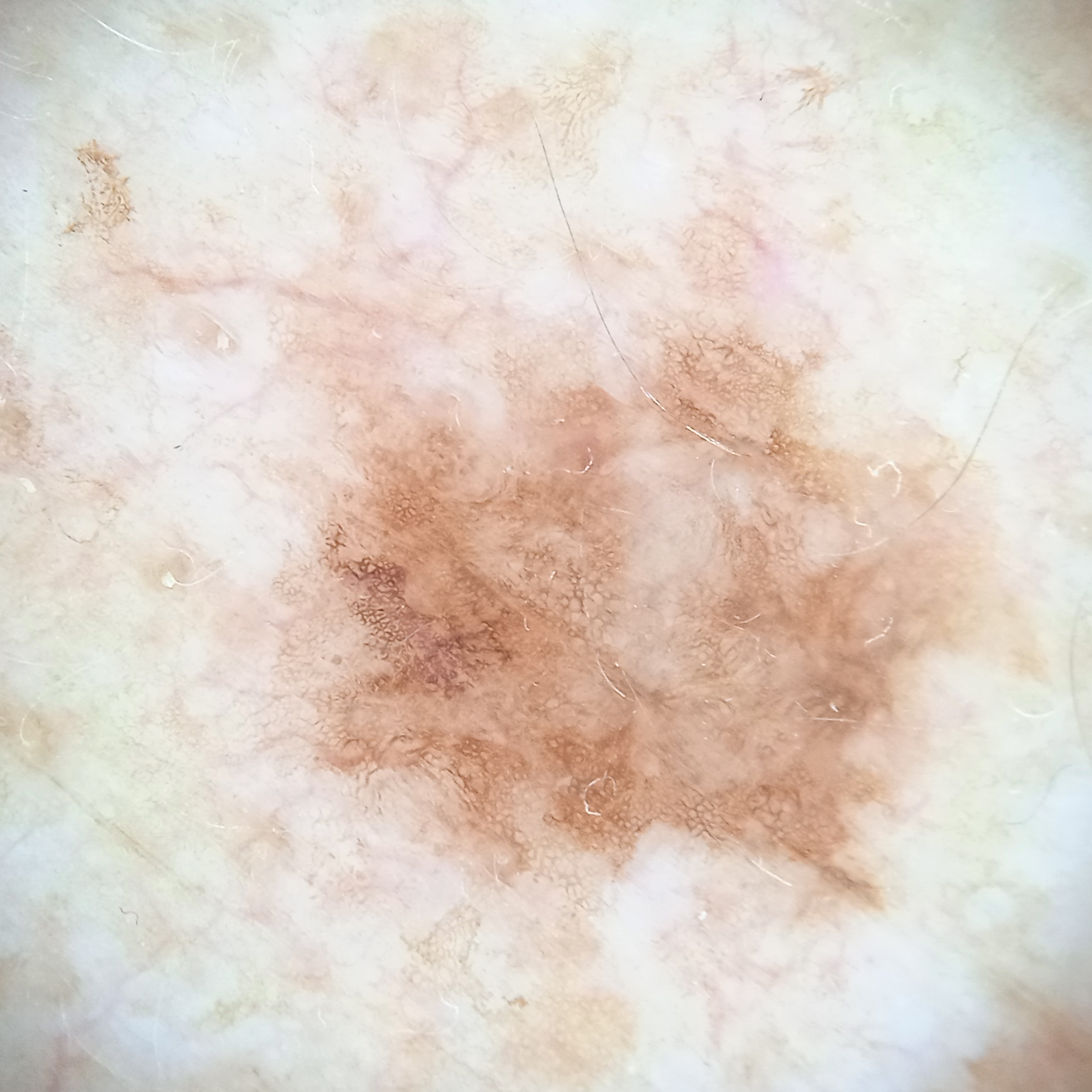The lesion was left diagnostically undetermined on review. Findings: The patient says their skin reddens with sun exposure. The patient reports a family history of skin cancer and a personal history of cancer. Dermoscopy of a skin lesion. Few moles overall by the patient's own estimate. A male patient age 81. Imaged for a research study, with no referral diagnosis recorded. The lesion is about 8 mm across.